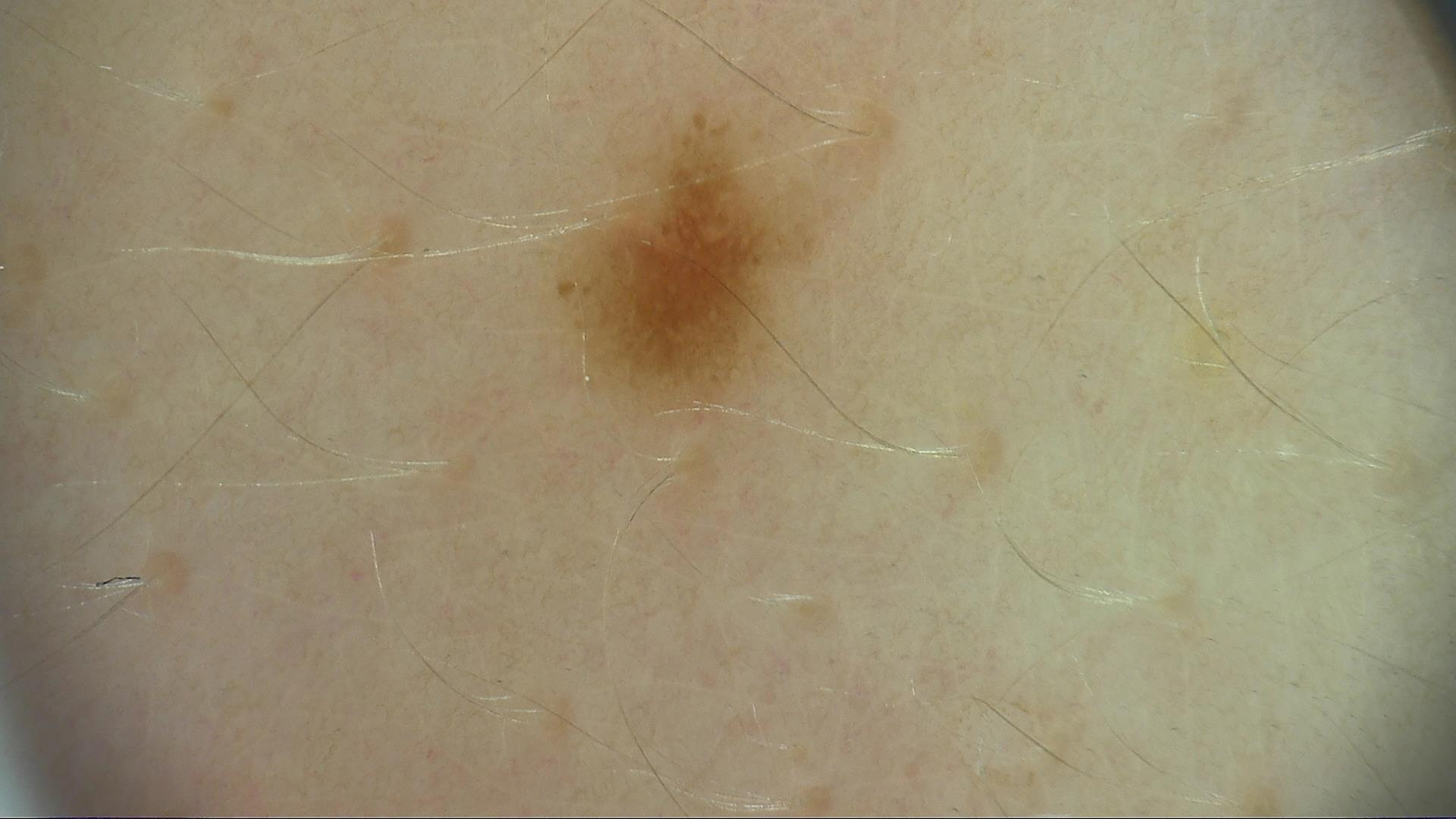A skin lesion imaged with a dermatoscope. Consistent with a benign lesion — a dysplastic junctional nevus.